A skin lesion imaged with a dermatoscope:
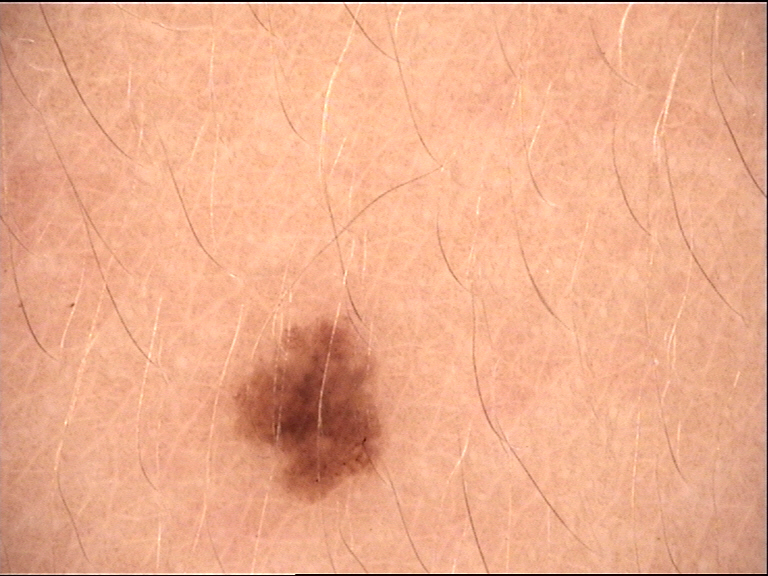The architecture is that of a banal lesion. Diagnosed as a junctional nevus.